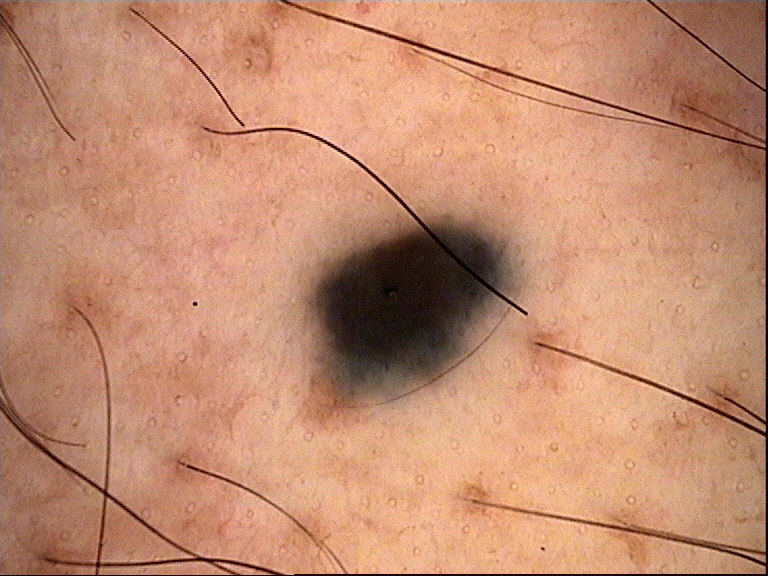{
  "image": "dermoscopy",
  "diagnosis": {
    "name": "blue nevus",
    "code": "bdb",
    "malignancy": "benign",
    "super_class": "melanocytic",
    "confirmation": "expert consensus"
  }
}